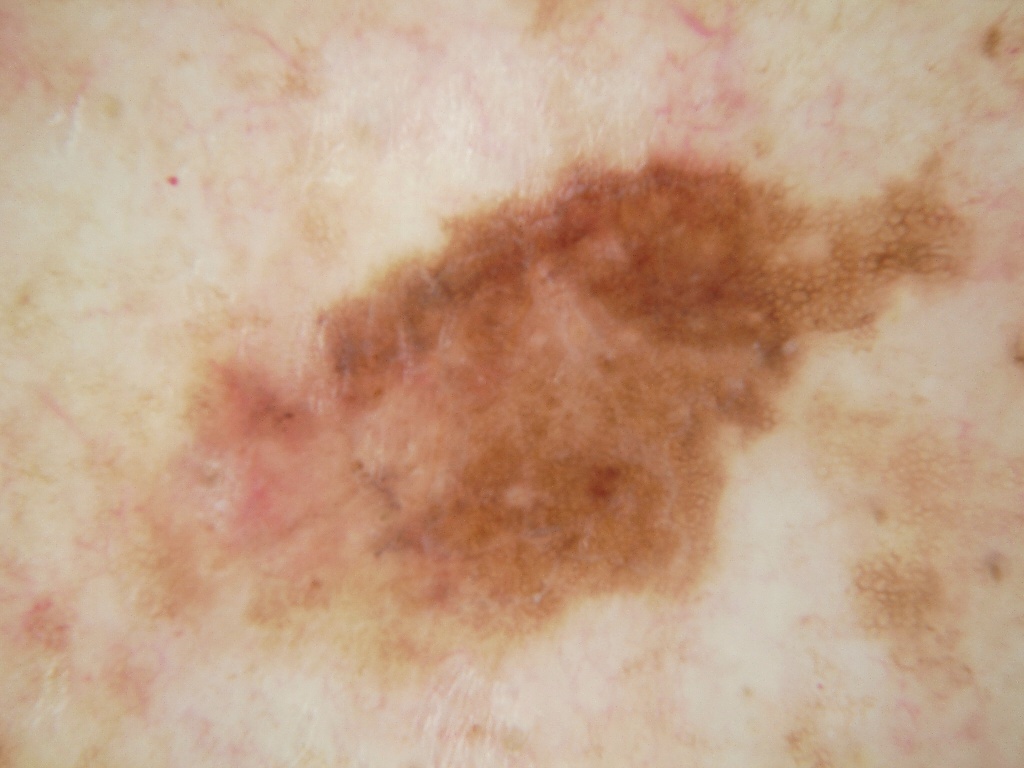A dermoscopy image of a single skin lesion. Dermoscopic review identifies pigment network. In (x1, y1, x2, y2) order, lesion location: bbox(124, 140, 982, 719). The diagnostic assessment was a melanocytic nevus.